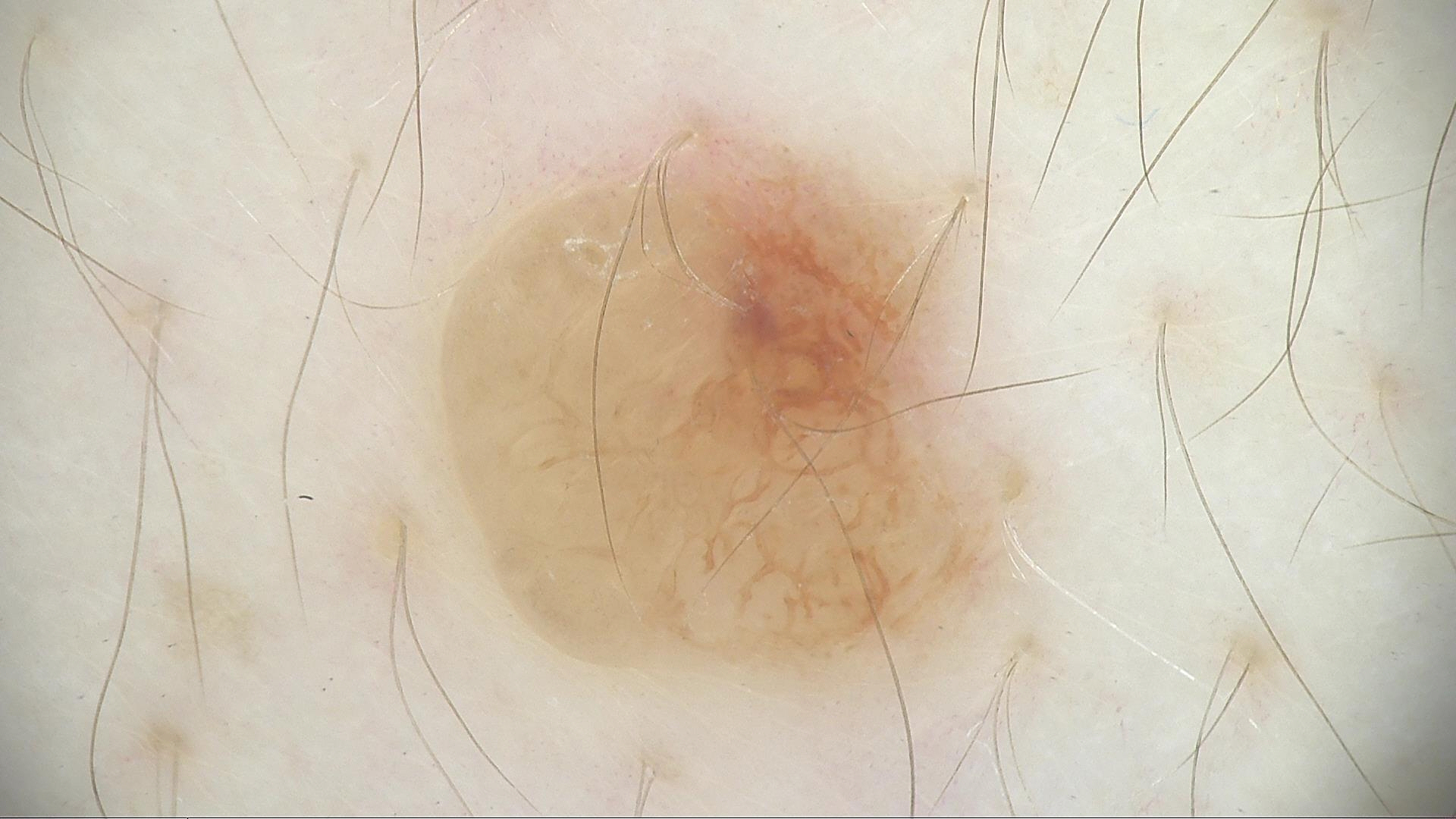{"image": "dermoscopy", "lesion_type": {"main_class": "banal", "pattern": "dermal"}, "diagnosis": {"name": "dermal nevus", "code": "db", "malignancy": "benign", "super_class": "melanocytic", "confirmation": "expert consensus"}}